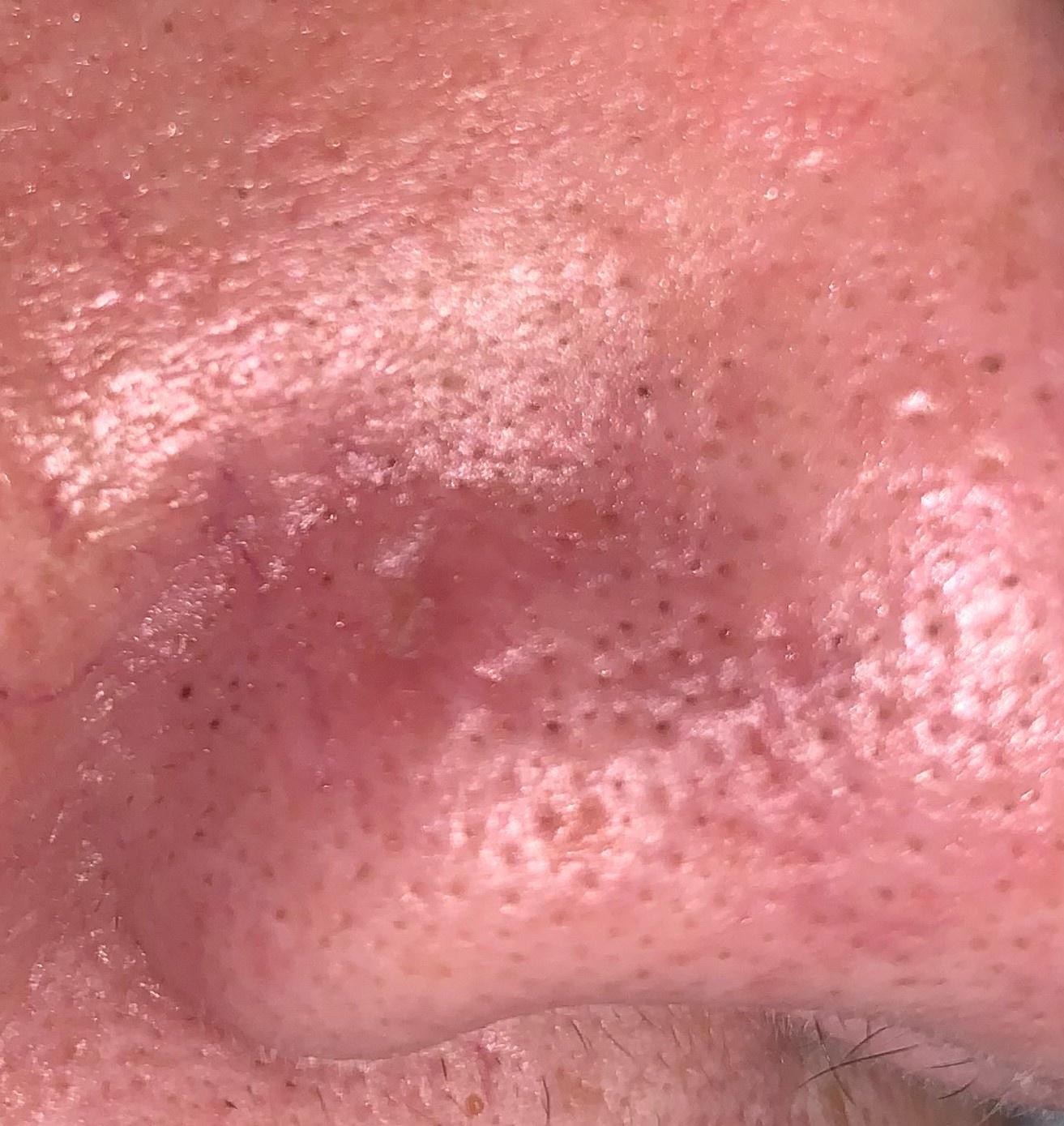Biopsy-confirmed as a basal cell carcinoma.